Self-categorized by the patient as a rash. The photo was captured at a distance. Associated systemic symptoms include fatigue. The lesion is associated with pain, bothersome appearance, enlargement and itching. The lesion is described as raised or bumpy. The condition has been present for less than one week: 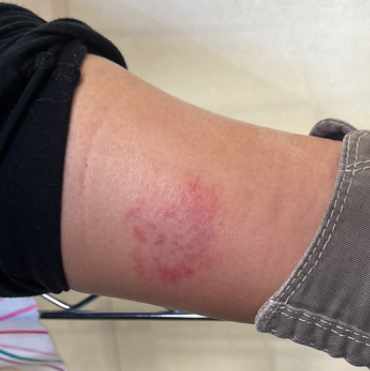Q: What is the differential diagnosis?
A: Irritant Contact Dermatitis (weight 0.67); Acute dermatitis, NOS (weight 0.33)